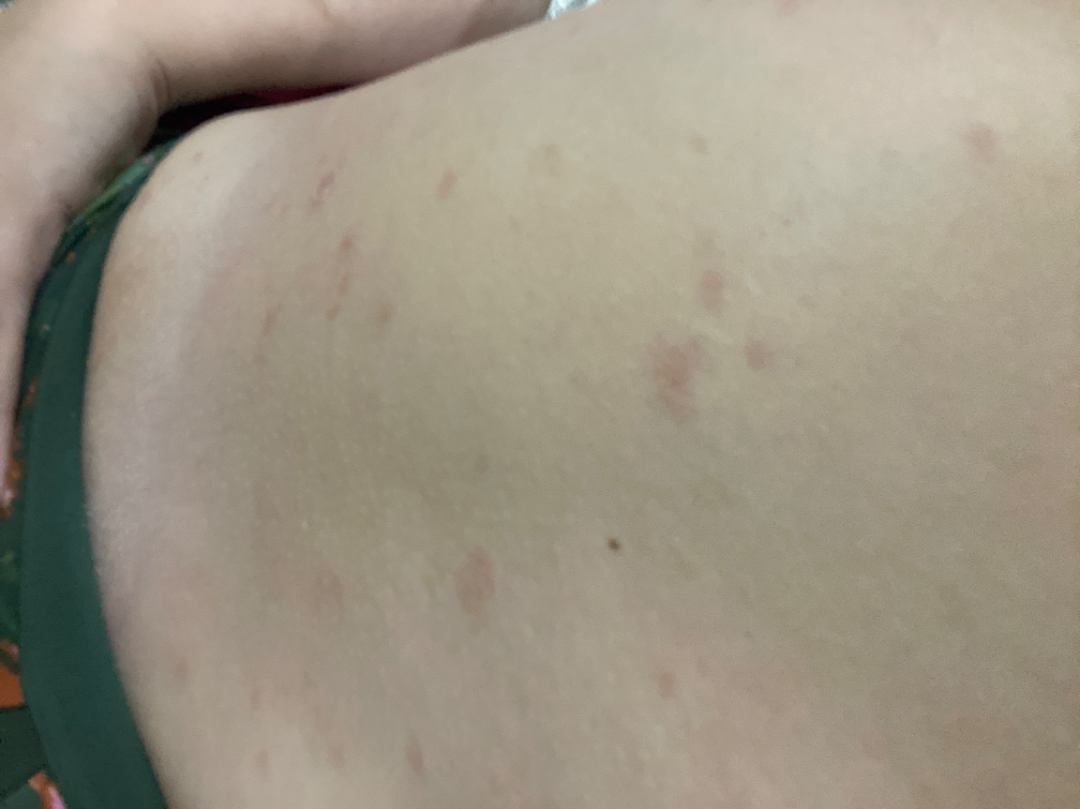<report>
  <body_site>front of the torso</body_site>
  <shot_type>at an angle</shot_type>
  <patient_category>a rash</patient_category>
  <patient>female, age 18–29</patient>
  <texture>rough or flaky, raised or bumpy</texture>
  <symptoms>pain, itching, enlargement, burning</symptoms>
  <differential>
    <tied_lead>Pityriasis rosea, Acute and chronic dermatitis, Pityriasis lichenoides</tied_lead>
  </differential>
</report>